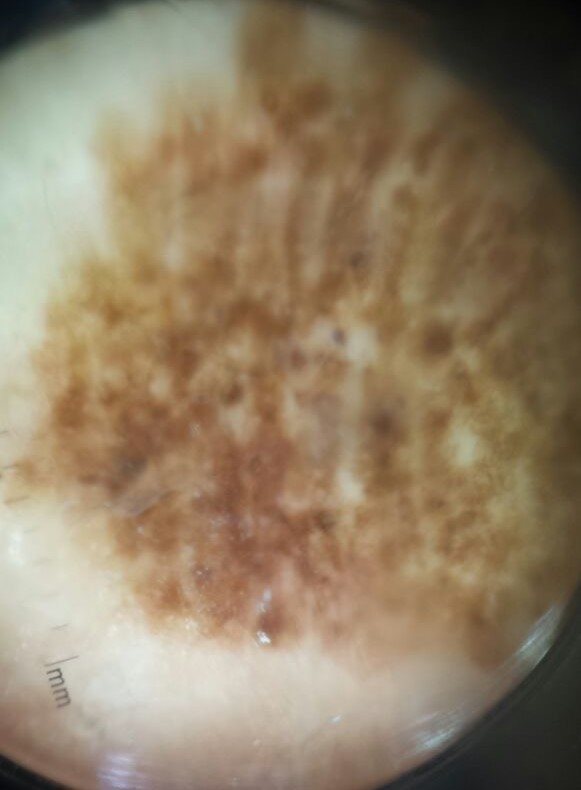Dermoscopy of a skin lesion. Diagnosed as a benign lesion — a congenital dysplastic compound nevus.